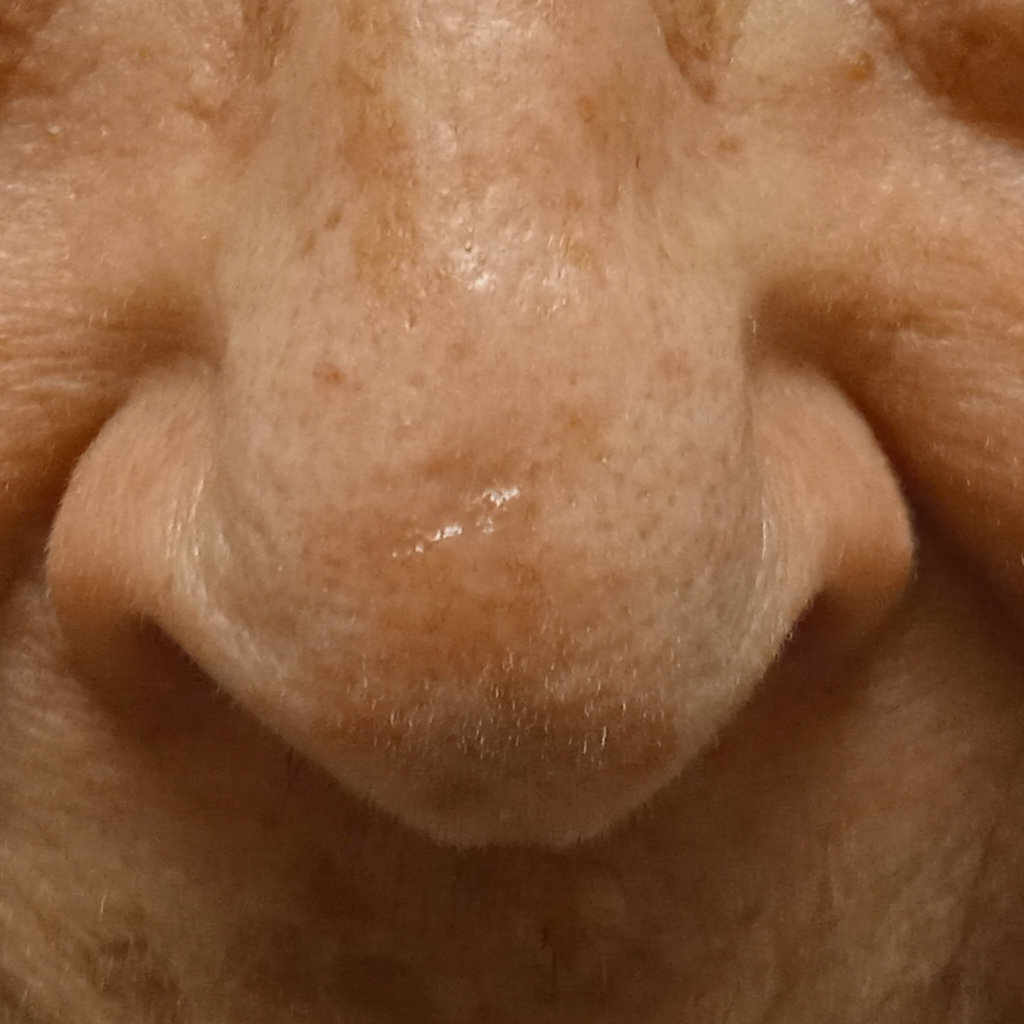The patient says their skin tans without first burning. Referred with a clinical suspicion of basal cell carcinoma. A female subject 84 years of age. A clinical photograph of a skin lesion. The patient describes having few moles overall. On a questionnaire the patient reported a personal history of cancer. Located on the face. The biopsy diagnosis was a basal cell carcinoma, following excision, with a measured thickness of 1.5 mm.